A female subject in their 50s:
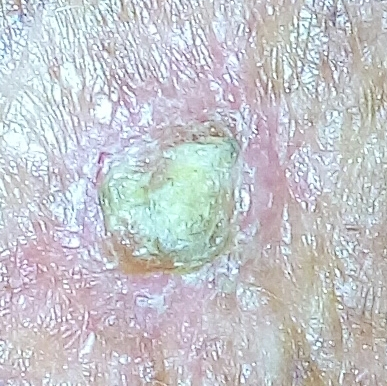Located on the chest. The patient describes that the lesion is elevated, has grown, and itches. Biopsy-confirmed as a basal cell carcinoma.